The affected area is the back of the torso and front of the torso · male subject, age 30–39 · no relevant lesion symptoms reported · the contributor reports the lesion is flat · present for one to three months · the photograph was taken at a distance:
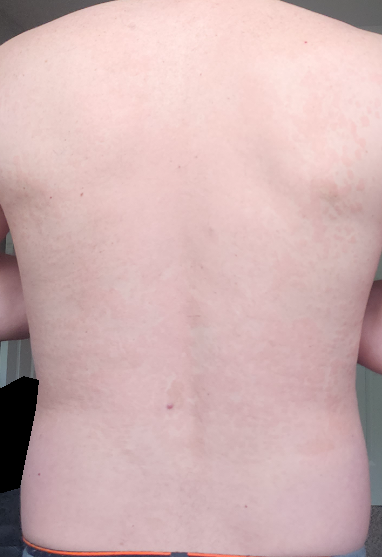Assessment:
On teledermatology review, Psoriasis (0.37); Pityriasis rosea (0.17); Tinea Versicolor (0.17); Parapsoriasis (0.14); Seborrheic Dermatitis (0.14).